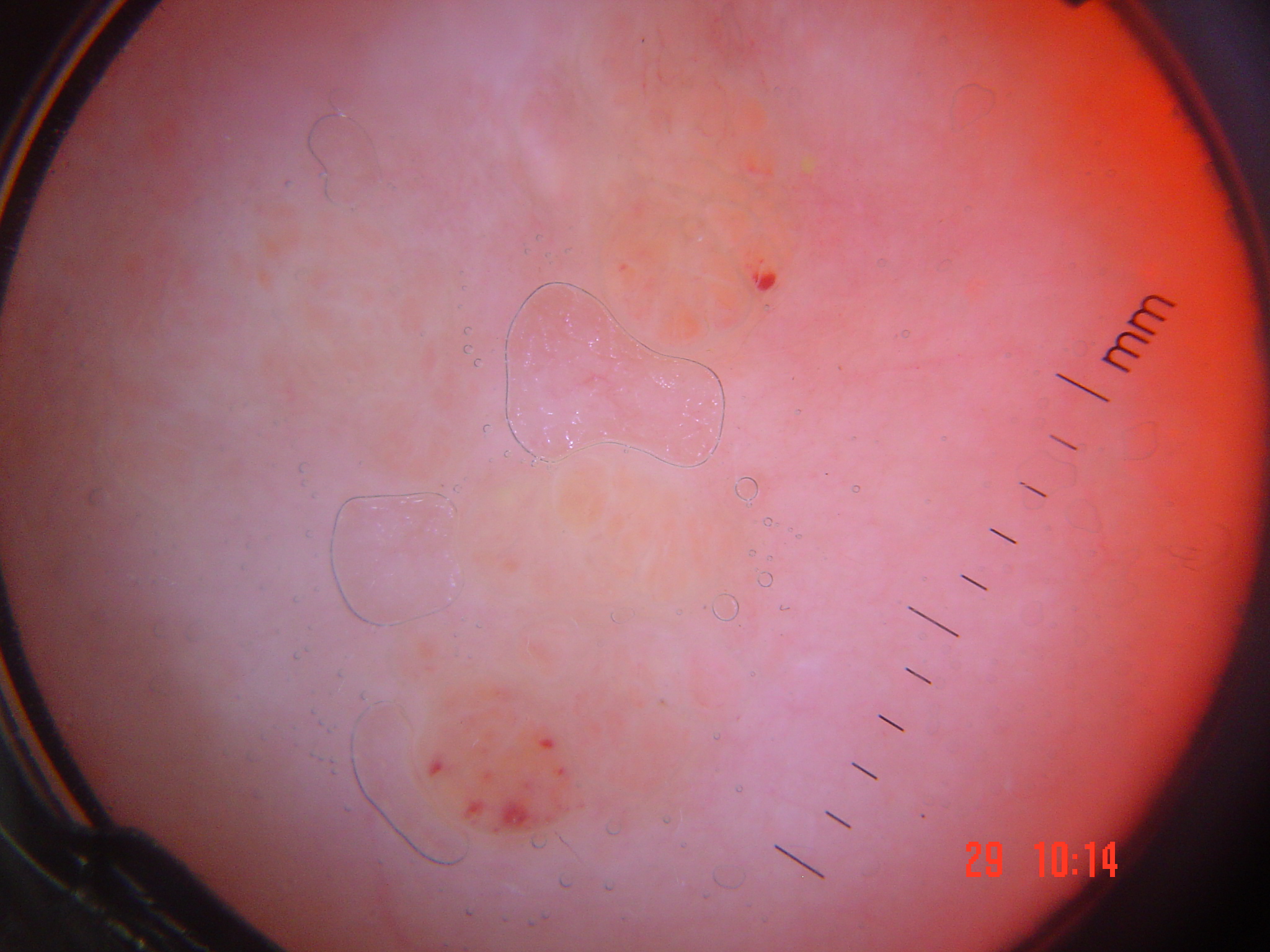subtype = vascular
assessment = lymphangioma (expert consensus)